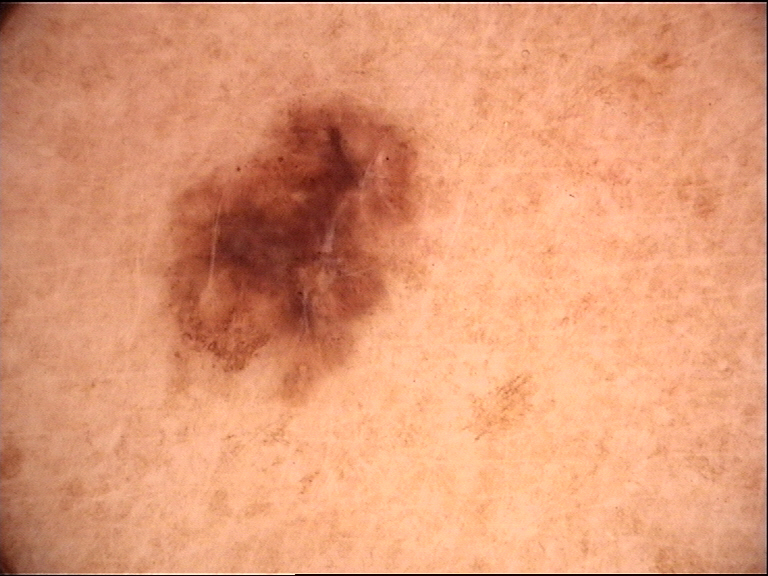Q: What is this lesion?
A: dysplastic junctional nevus (expert consensus)